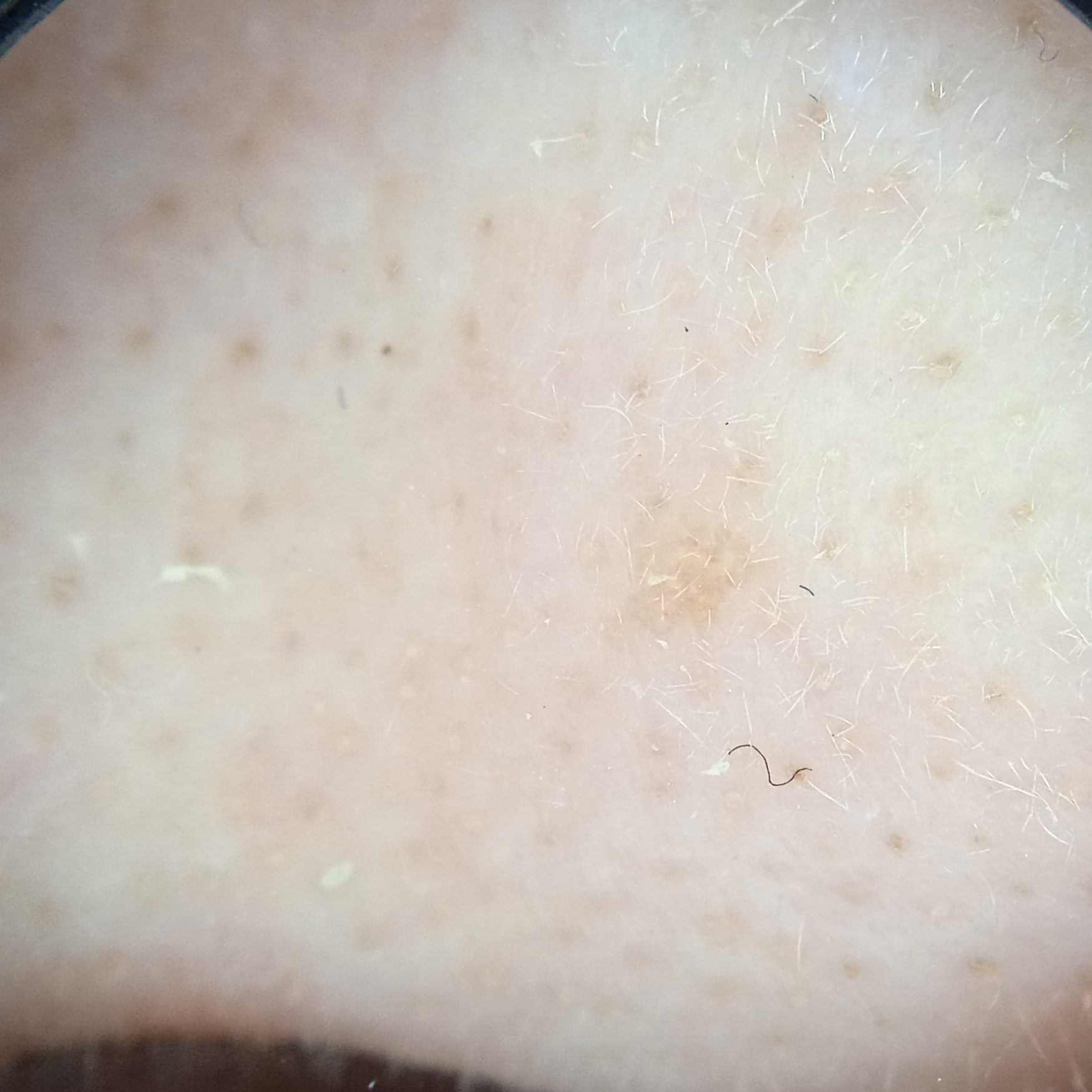Q: What are the relevant risk factors?
A: a personal history of skin cancer, a personal history of cancer, no family history of skin cancer, no immunosuppression
Q: What is the referral context?
A: clinical suspicion of basal cell carcinoma
Q: What is the imaging modality?
A: dermatoscopic image
Q: How does the patient's skin react to sun?
A: skin reddens with sun exposure
Q: Tell me about the patient.
A: female, 71 years old
Q: What is the patient's nevus burden?
A: few melanocytic nevi overall
Q: Where is the lesion?
A: the face
Q: Lesion size?
A: 7.3 mm
Q: What was the diagnosis?
A: actinic keratosis (dermatologist consensus)